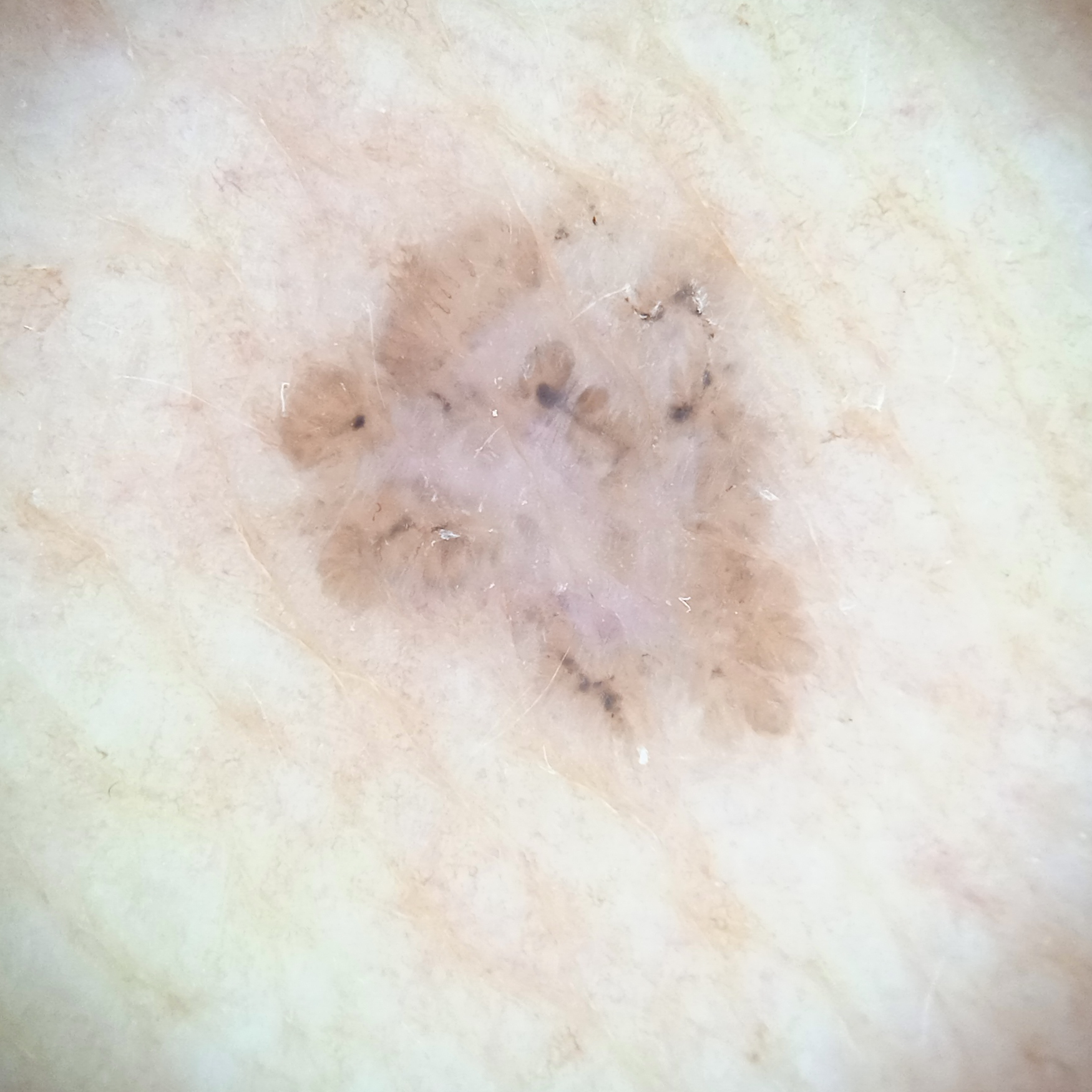Summary:
Referred with a clinical suspicion of basal cell carcinoma. A skin lesion imaged with a dermatoscope. A female patient 60 years old. The lesion involves the torso. Measuring roughly 7.2 mm.
Conclusion:
The diagnostic impression was a basal cell carcinoma.